The photograph was taken at a distance · the affected area is the top or side of the foot · the patient is 50–59, female — 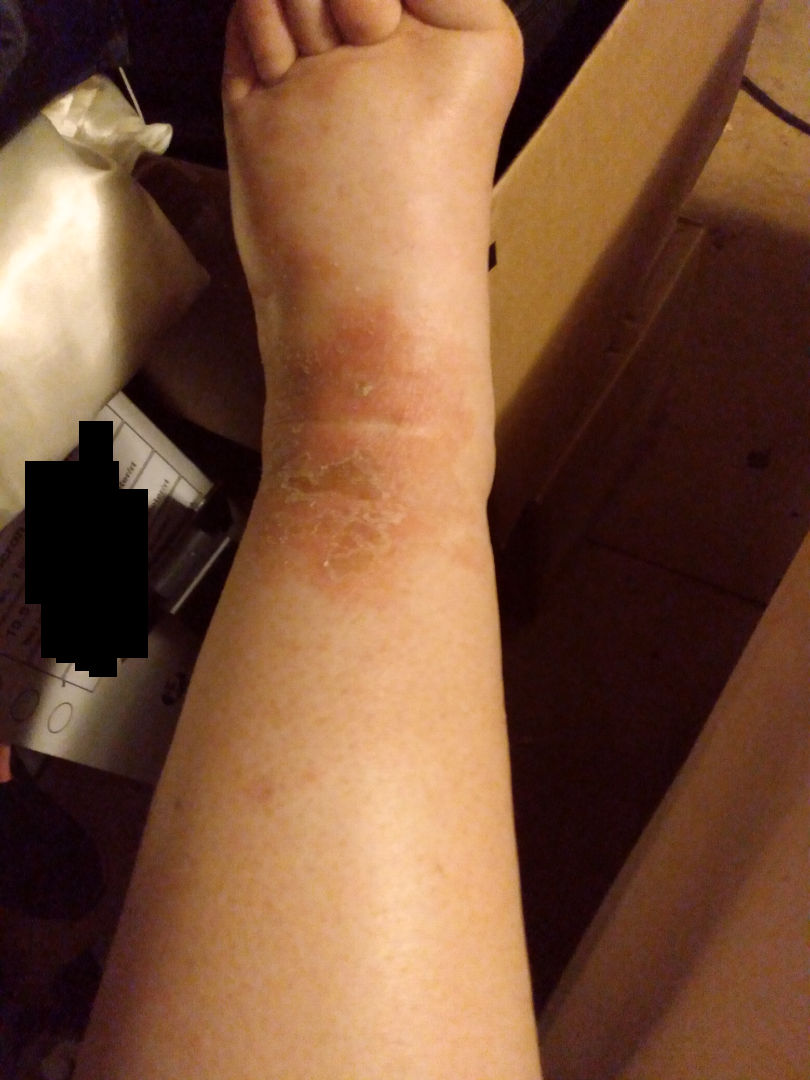systemic_symptoms: none reported
symptoms:
  - bothersome appearance
  - burning
  - itching
patient_category: a rash
duration: three to twelve months
skin_tone:
  fitzpatrick: I
  monk_skin_tone:
    - 3
    - 4
texture: rough or flaky
differential:
  leading:
    - Eczema
  unlikely:
    - Impetigo
    - Stasis Dermatitis
    - Ichthyosiform dermatosis